The patient described the issue as a rash. The patient indicates the condition has been present for three to twelve months. The lesion is described as raised or bumpy. The leg, arm, back of the hand and back of the torso are involved. Skin tone: self-reported Fitzpatrick IV; human graders estimated MST 1 (US pool) or 2 (India pool). The subject is 50–59, female. The photograph is a close-up of the affected area. The patient also reports fatigue and joint pain:
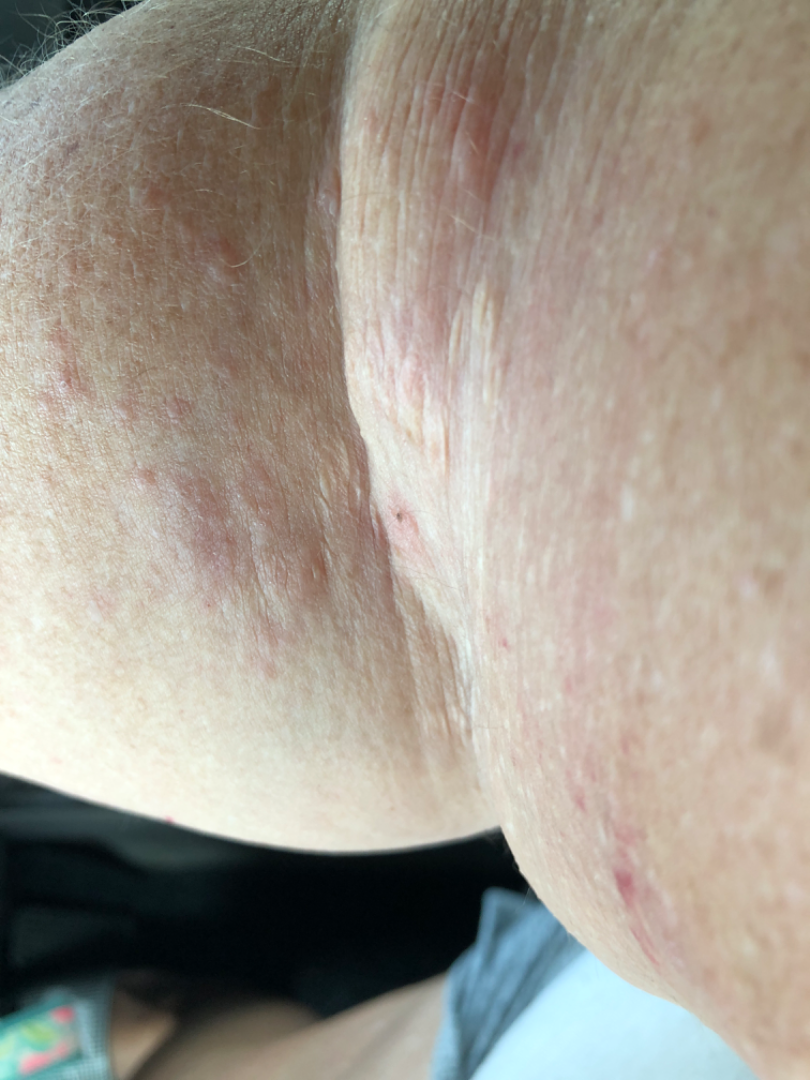Q: Could the case be diagnosed?
A: indeterminate from the photograph